On a questionnaire the patient reported a personal history of cancer, a family history of skin cancer, a personal history of skin cancer, no sunbed use, and no immunosuppression; the patient says their skin reddens with sun exposure; the patient describes having numerous moles; a female patient 54 years of age; a clinical close-up of a skin lesion; collected as part of a research study, without a referral diagnosis: 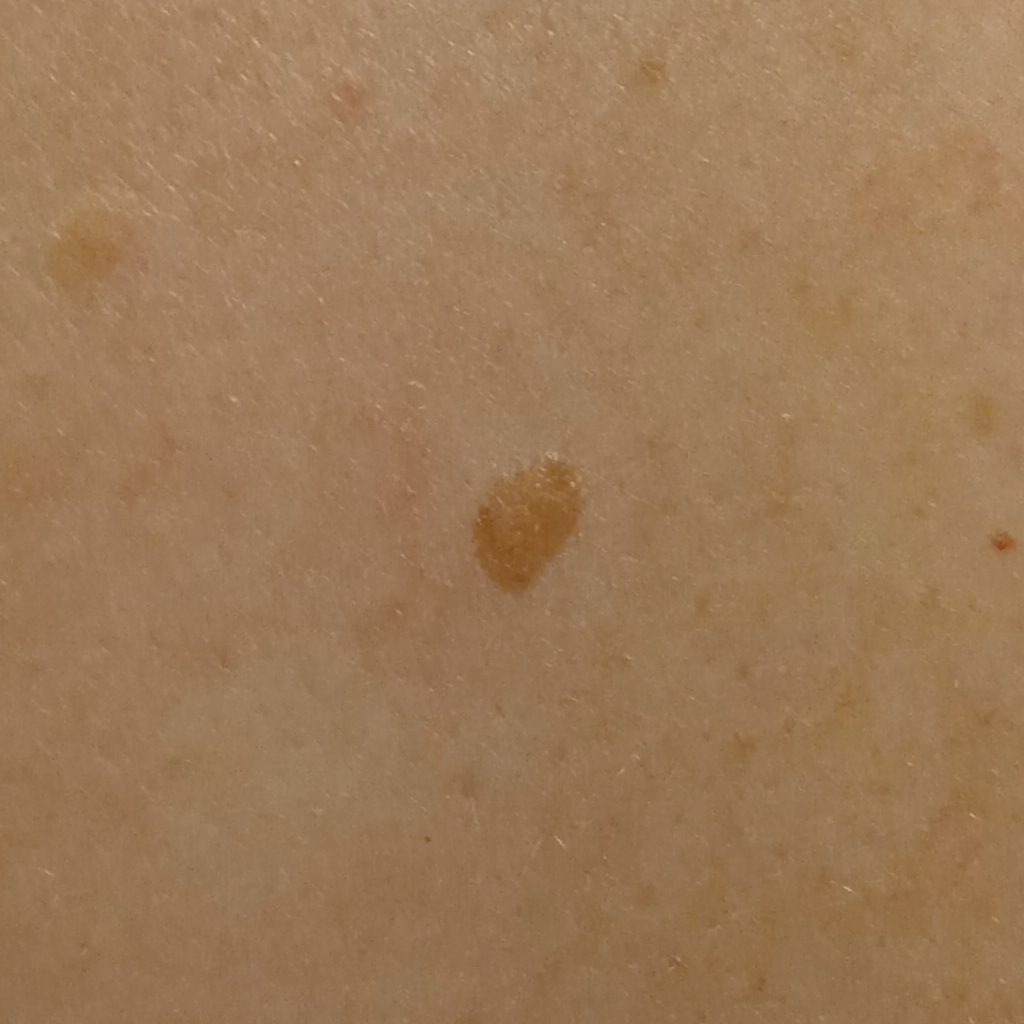Q: Where is the lesion?
A: the back
Q: How large is the lesion?
A: 5.5 mm
Q: What was the diagnosis?
A: seborrheic keratosis (dermatologist consensus)